Texture is reported as raised or bumpy and fluid-filled. Reported lesion symptoms include bothersome appearance, darkening and enlargement. The patient considered this a rash. Present for about one day. This image was taken at an angle. The front of the torso, back of the torso and head or neck are involved.
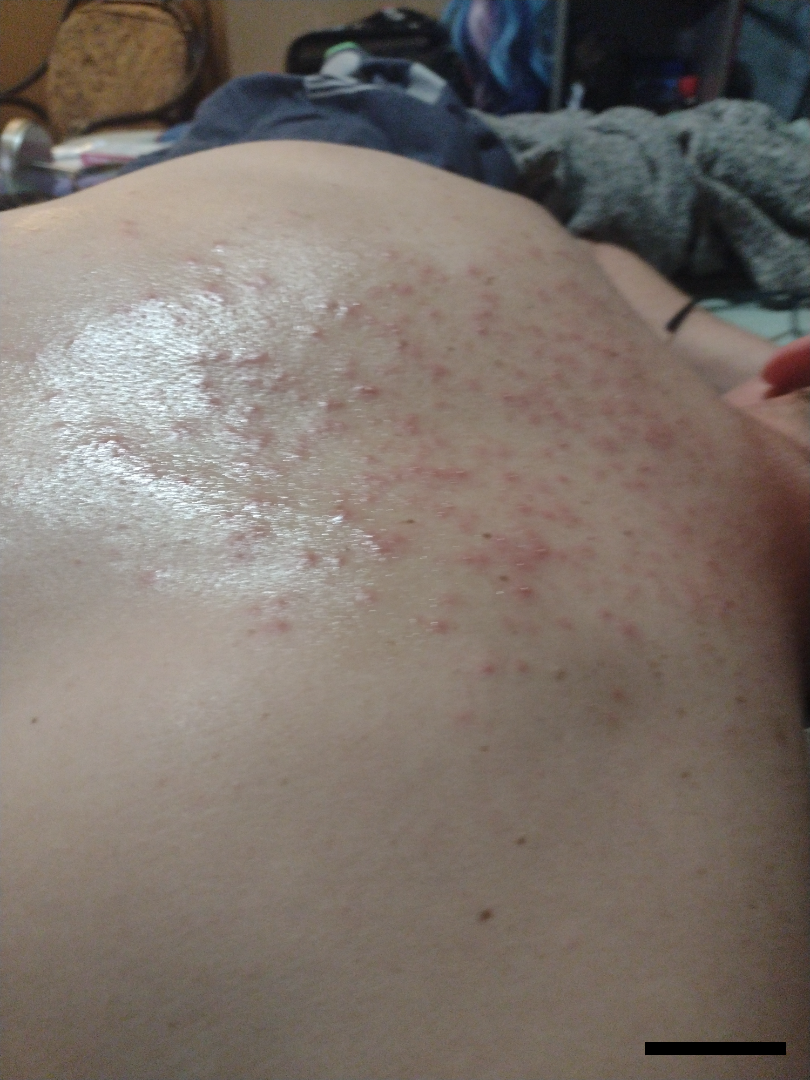Folliculitis (primary); Miliaria (considered).